The subject is a female aged 30–39. This image was taken at a distance. The affected area is the arm.
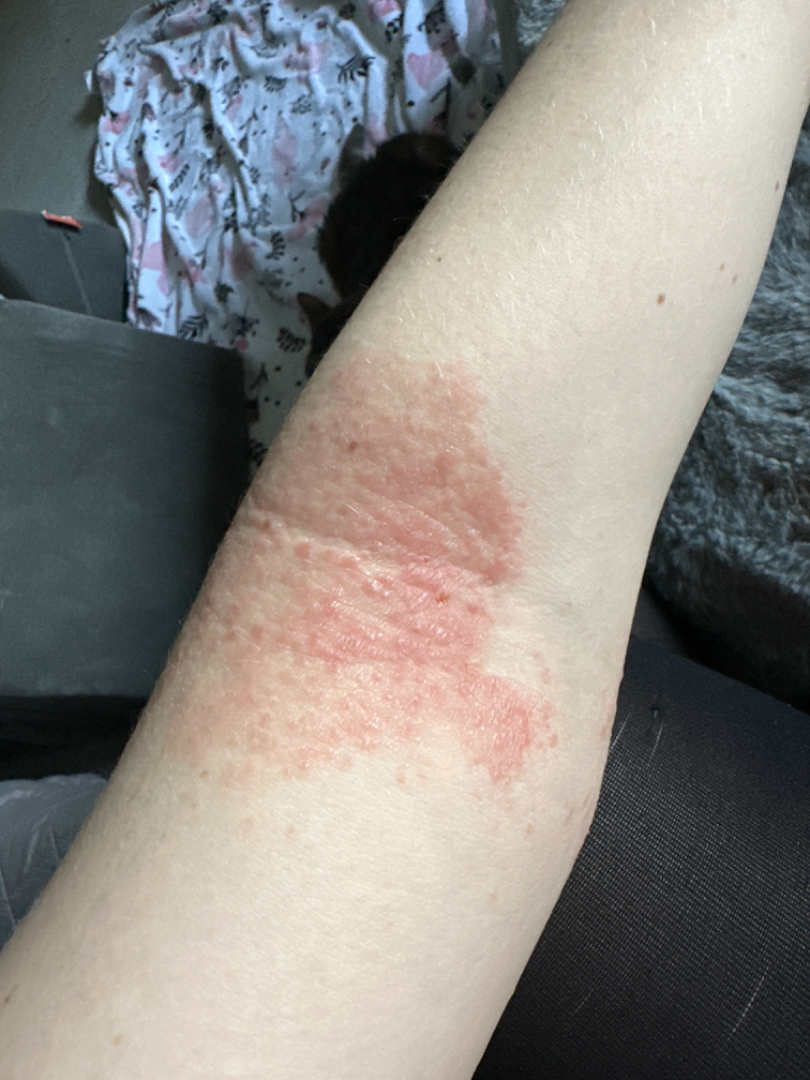Case summary:
• texture: raised or bumpy
• assessment: Eczema (69%); Tinea (19%); Allergic Contact Dermatitis (12%)